The patient notes the lesion is raised or bumpy · the photograph was taken at a distance · reported duration is about one day · the lesion is associated with itching and enlargement · the patient described the issue as a rash · female patient, age 18–29 · located on the arm.
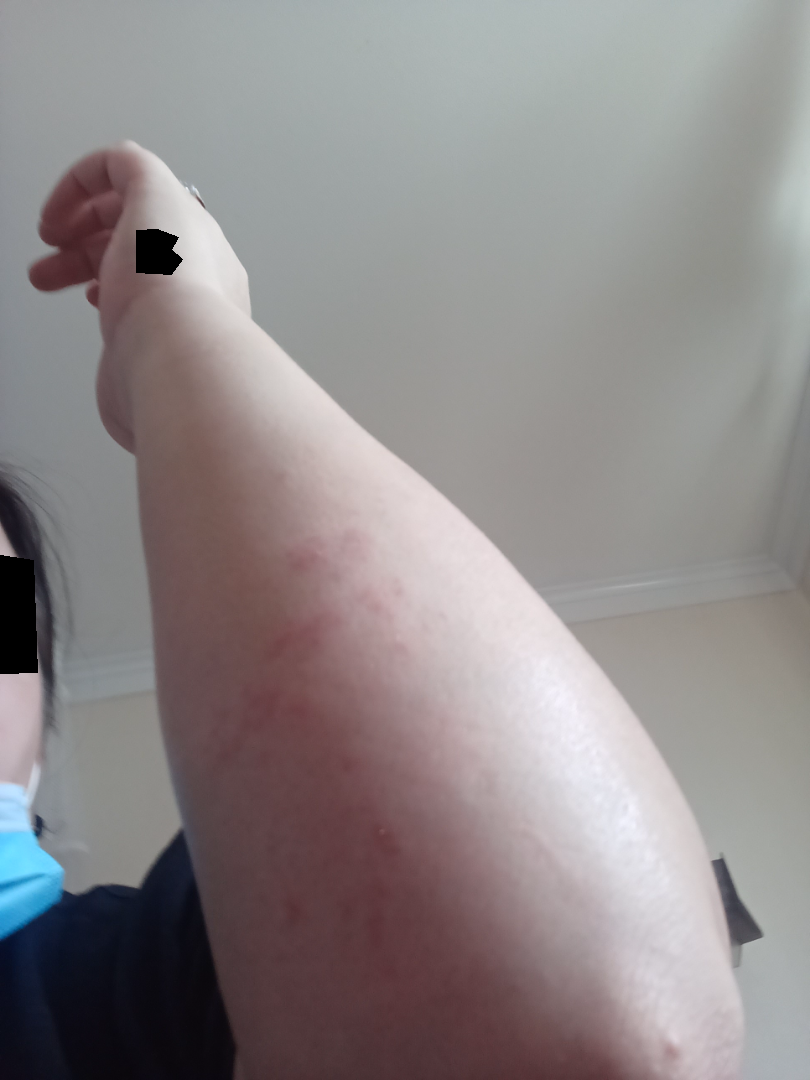diagnostic considerations: the differential, in no particular order, includes Eczema and Allergic Contact Dermatitis